The contributor reports associated joint pain and fatigue; the contributor reports the condition has been present for one to four weeks; close-up view; female subject, age 30–39; the patient considered this a nail problem; symptoms reported: bothersome appearance — 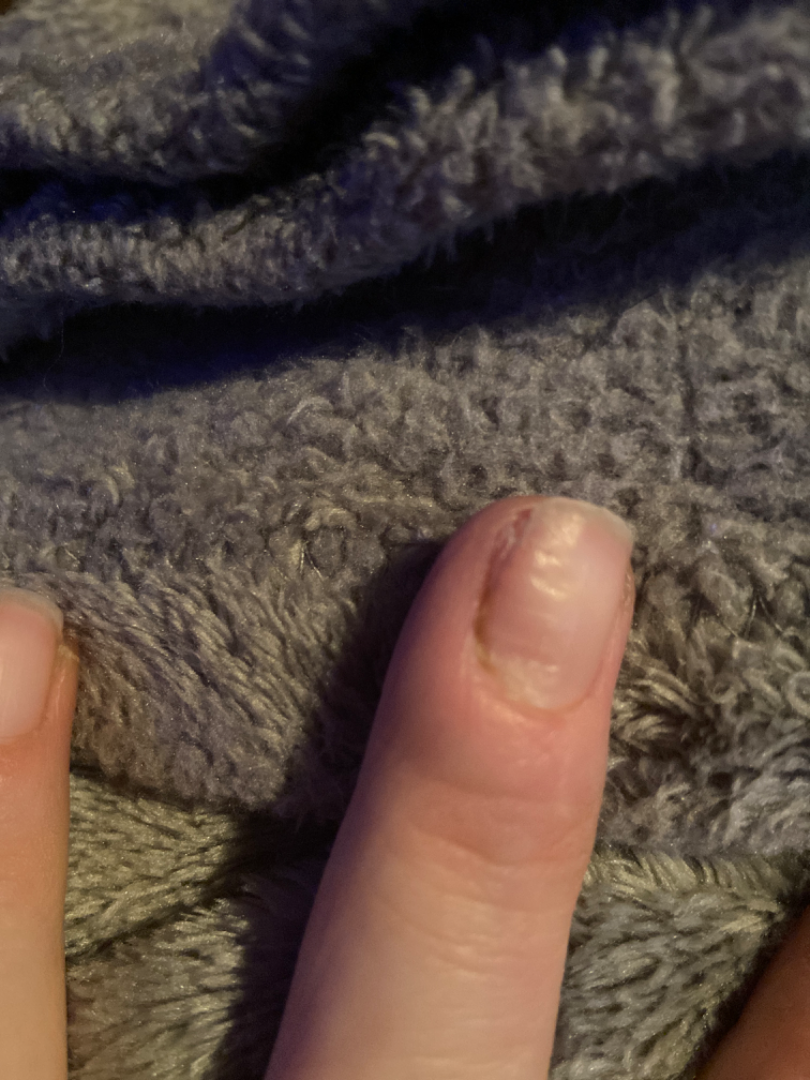Case summary:
– differential: the favored diagnosis is Nail dystrophy; possibly Nail pitting; also consider Nail dystrophy due to trauma; a more distant consideration is Paronychia; less likely is Onychomycosis